A dermoscopic image of a skin lesion:
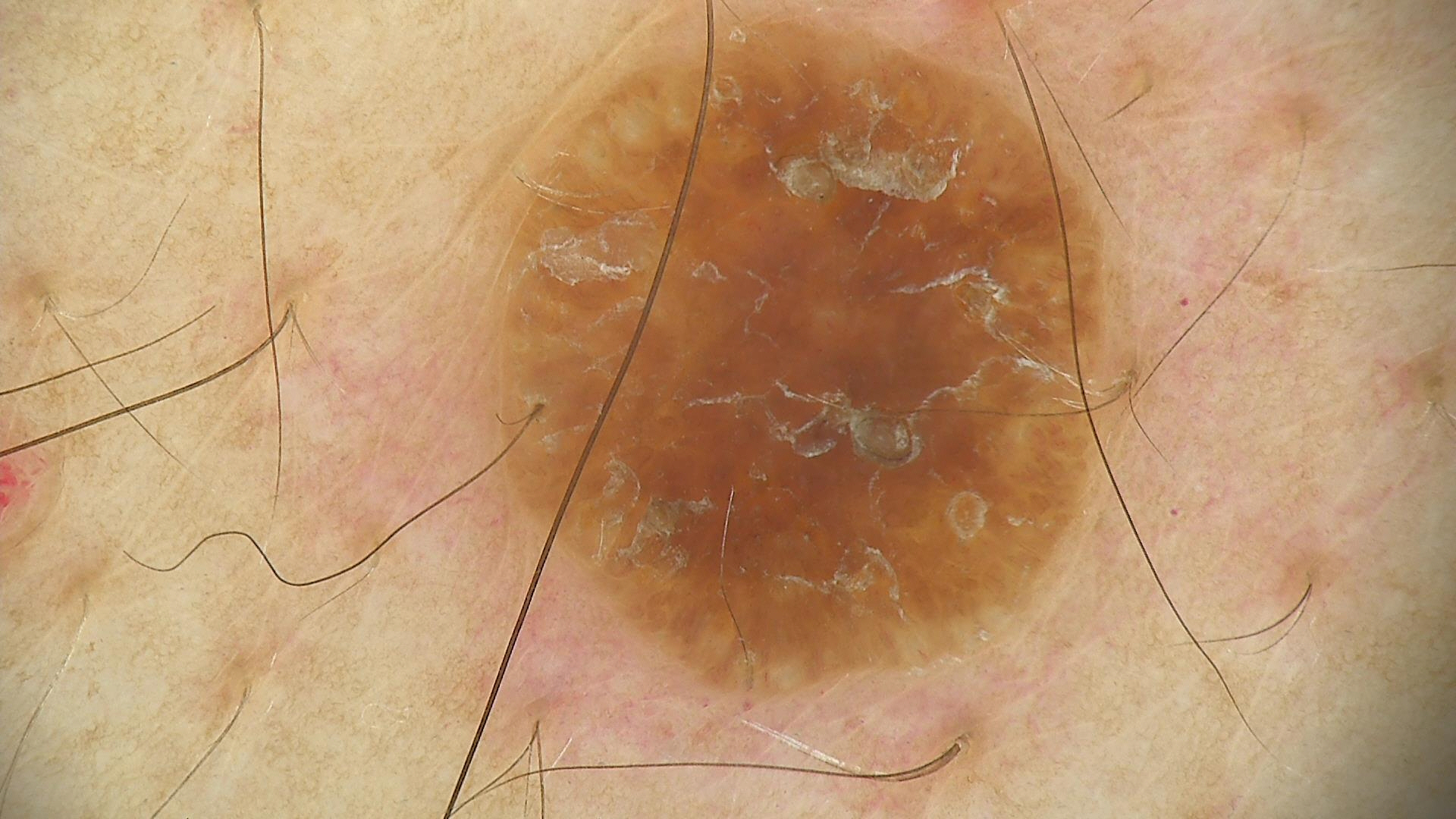diagnosis: seborrheic keratosis (expert consensus).